A dermatoscopic image of a skin lesion.
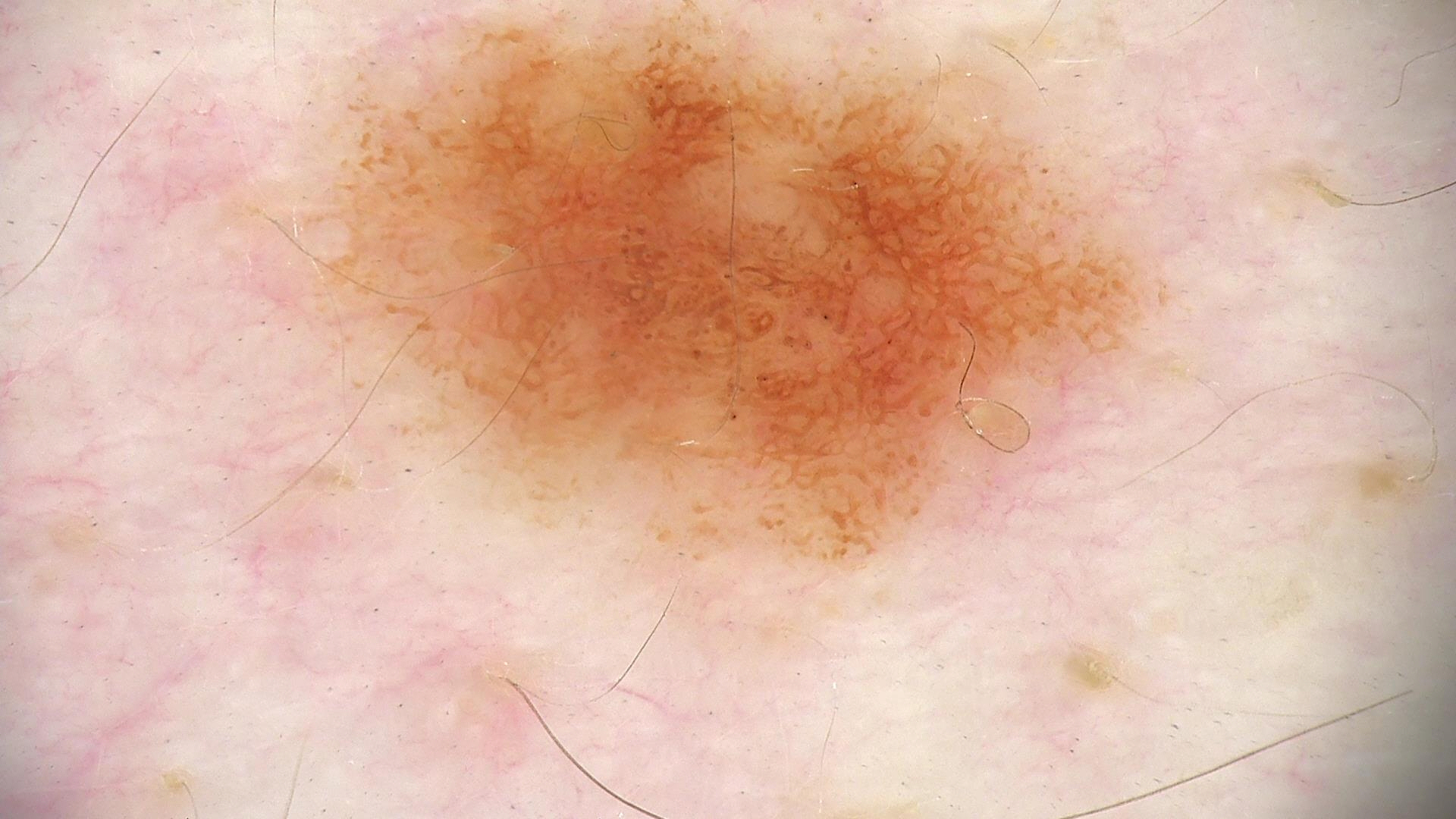Case:
* label: dysplastic junctional nevus (expert consensus)